The photograph is a close-up of the affected area; the lesion involves the back of the hand:
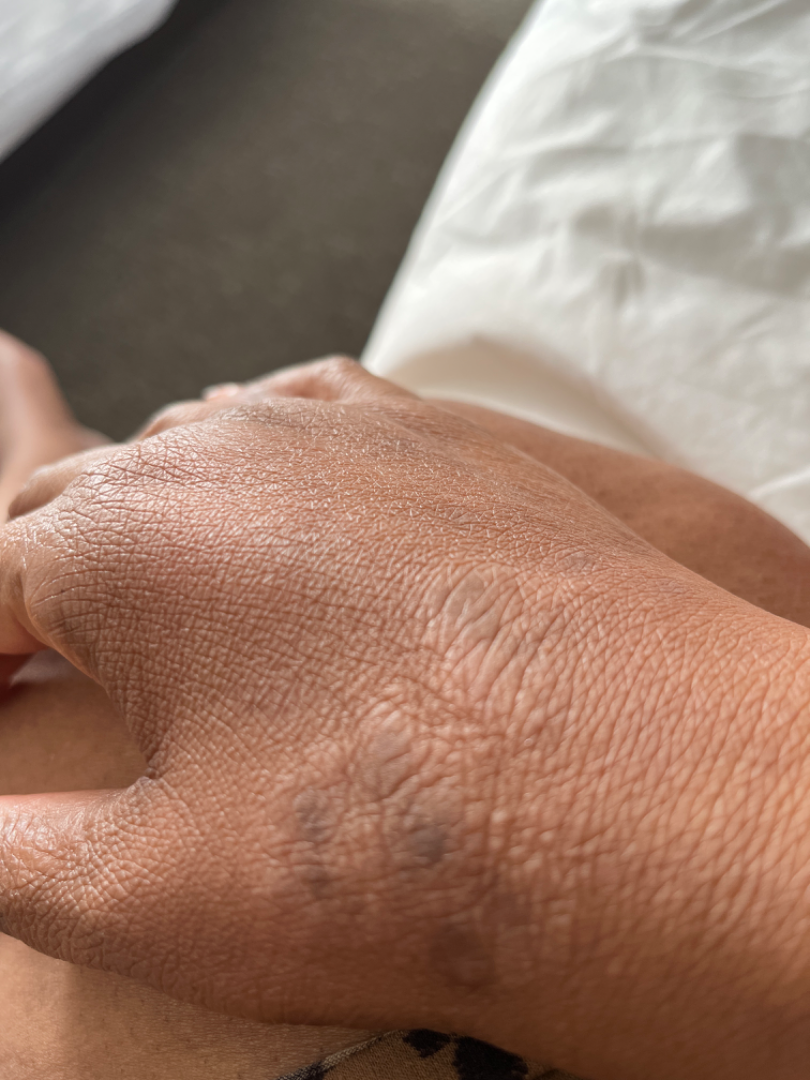Background: The patient considered this a rash. The condition has been present for one to four weeks. Findings: The reviewing dermatologist's impression was: most consistent with Lichen Simplex Chronicus; also raised was Cutaneous sarcoidosis; a more distant consideration is Tinea.